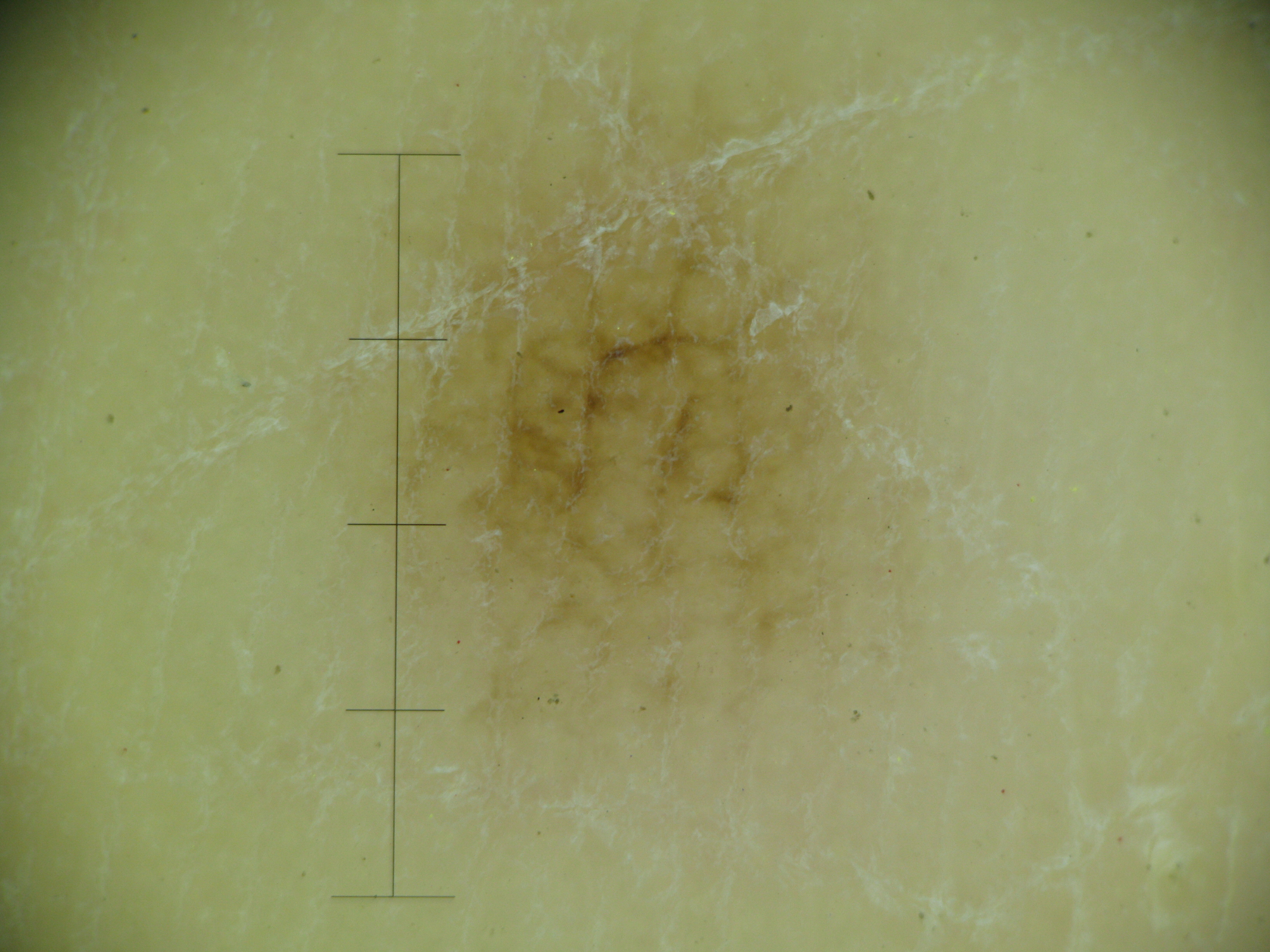diagnostic label=acral junctional nevus (expert consensus)